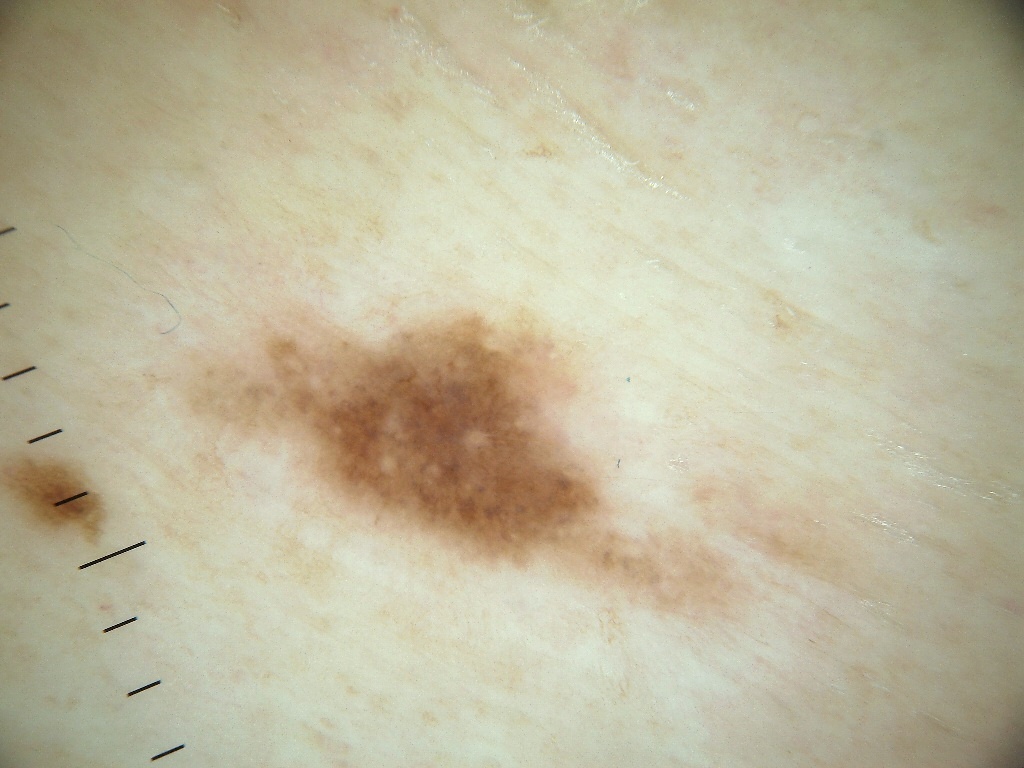The subject is a female in their mid- to late 40s. This is a dermoscopic photograph of a skin lesion. With coordinates (x1, y1, x2, y2), the lesion is bounded by <box>177, 312, 730, 609</box>. Dermoscopic assessment notes no milia-like cysts, streaks, negative network, pigment network, or globules. Diagnosed as a melanocytic nevus, a benign skin lesion.